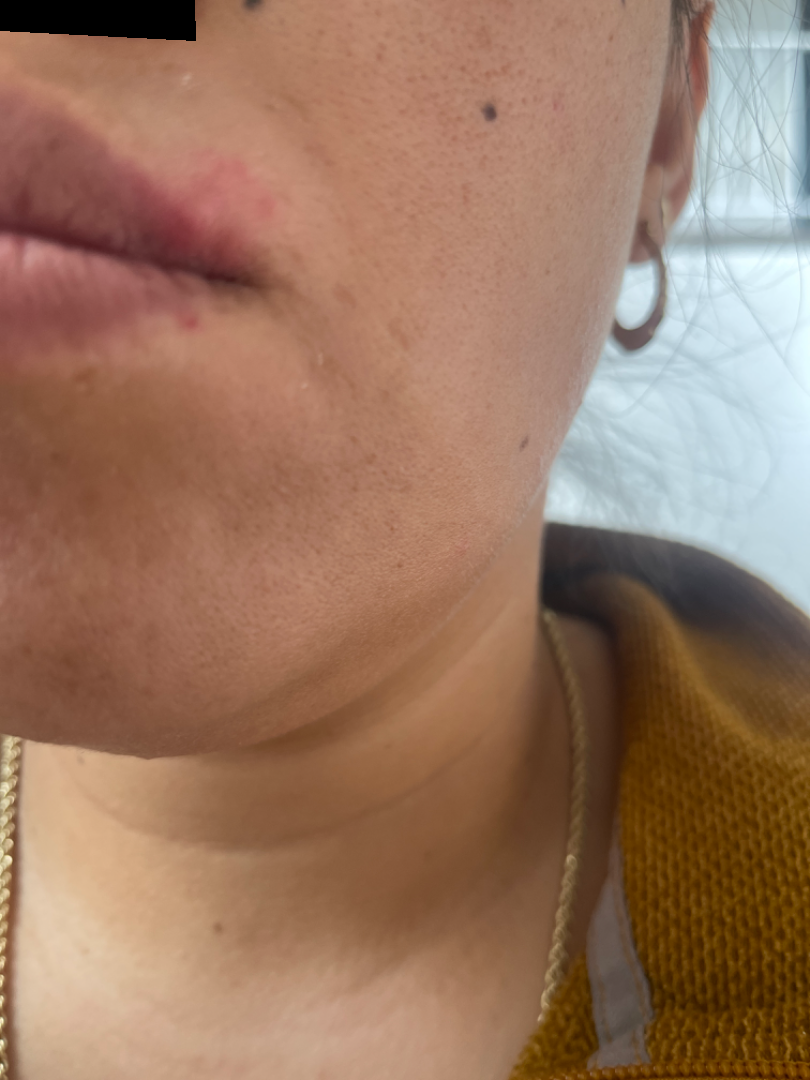patient's own categorization: a rash | subject: female, age 30–39 | patient-reported symptoms: itching | constitutional symptoms: none reported | onset: about one day | described texture: raised or bumpy | photo taken: at a distance | differential diagnosis: the leading consideration is Herpes Simplex; also raised was Allergic Contact Dermatitis.